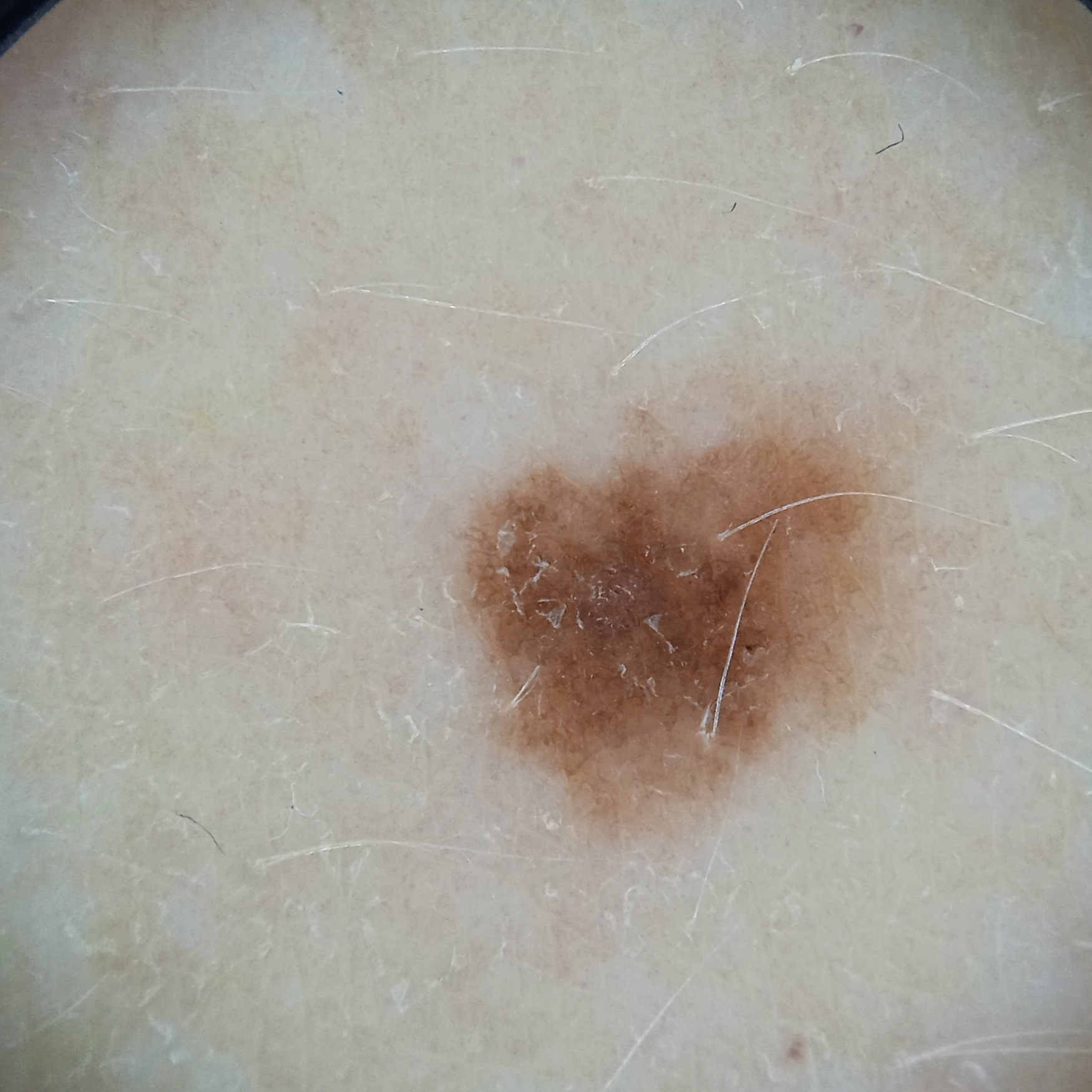Q: Why was this imaged?
A: research study (no referral diagnosis)
Q: What is the patient's nevus burden?
A: a moderate number of melanocytic nevi
Q: How does the patient's skin react to sun?
A: skin reddens with sun exposure
Q: What are the relevant risk factors?
A: a personal history of skin cancer
Q: Tell me about the patient.
A: female, aged 50
Q: What kind of image is this?
A: dermoscopy
Q: Where is the lesion?
A: the torso
Q: How large is the lesion?
A: 5.4 mm
Q: What was the diagnosis?
A: melanocytic nevus (dermatologist consensus)